This is a close-up image — 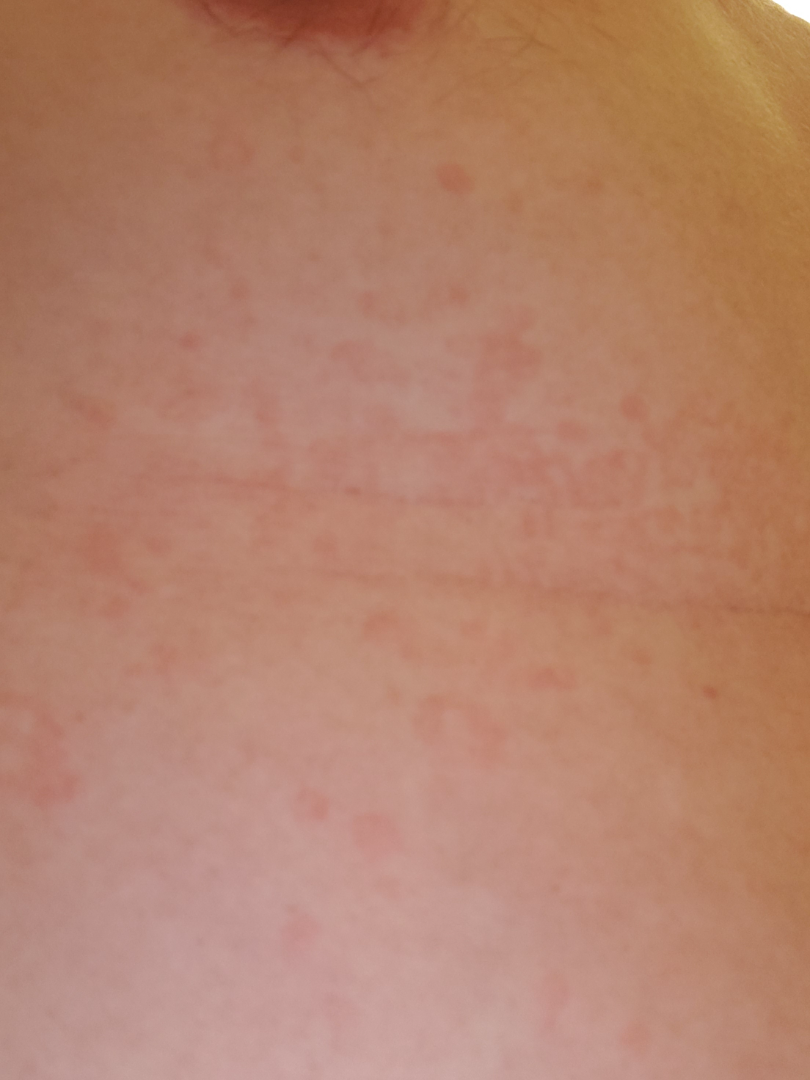Q: What is the dermatologist's impression?
A: most consistent with Tinea Versicolor